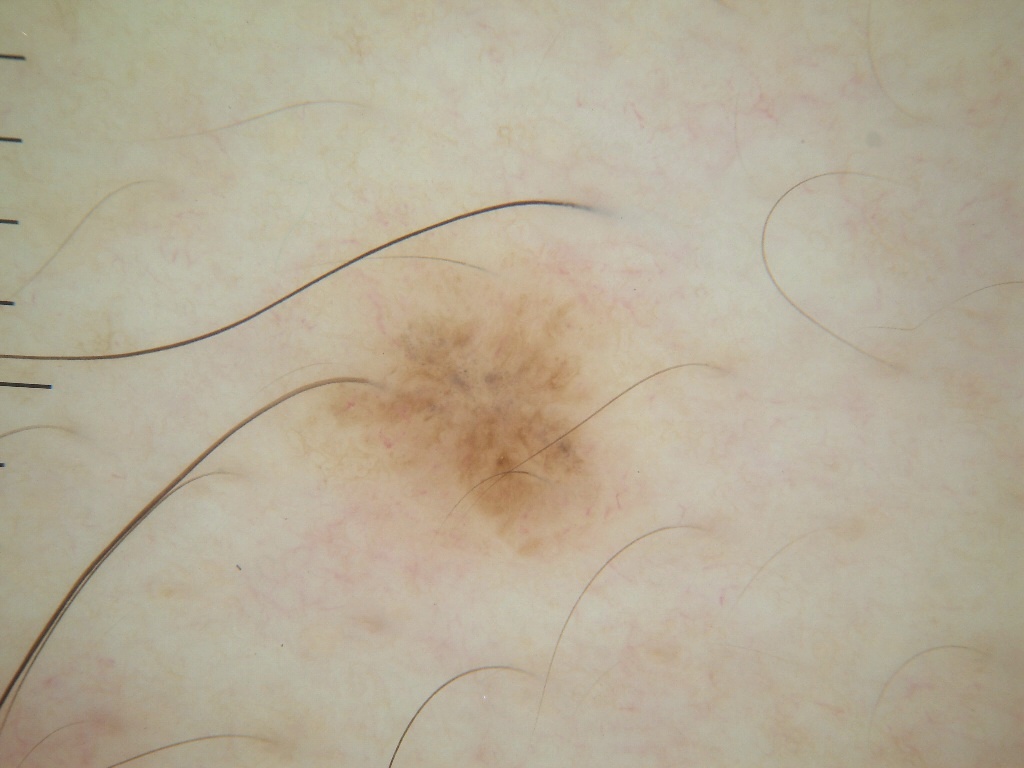image — dermoscopic image | bounding box — x1=265, y1=223, x2=641, y2=571 | diagnosis — a melanocytic nevus.